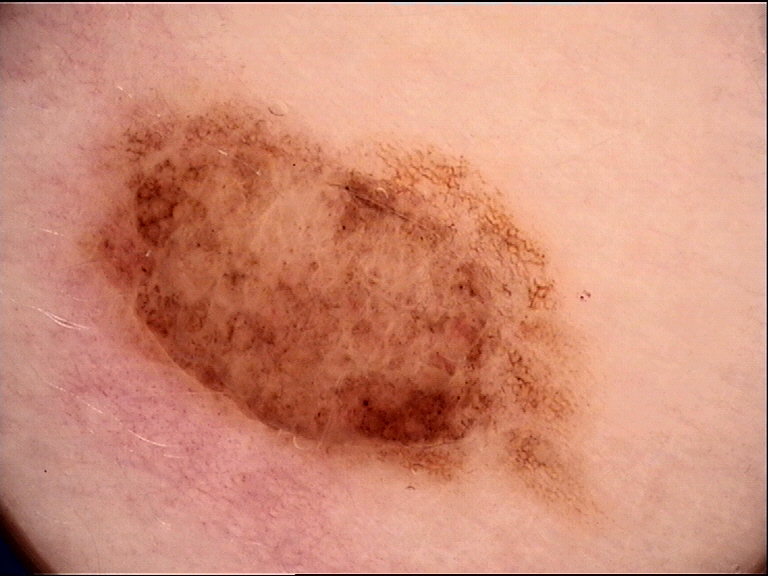Case:
– modality — dermoscopy
– label — compound nevus (expert consensus)